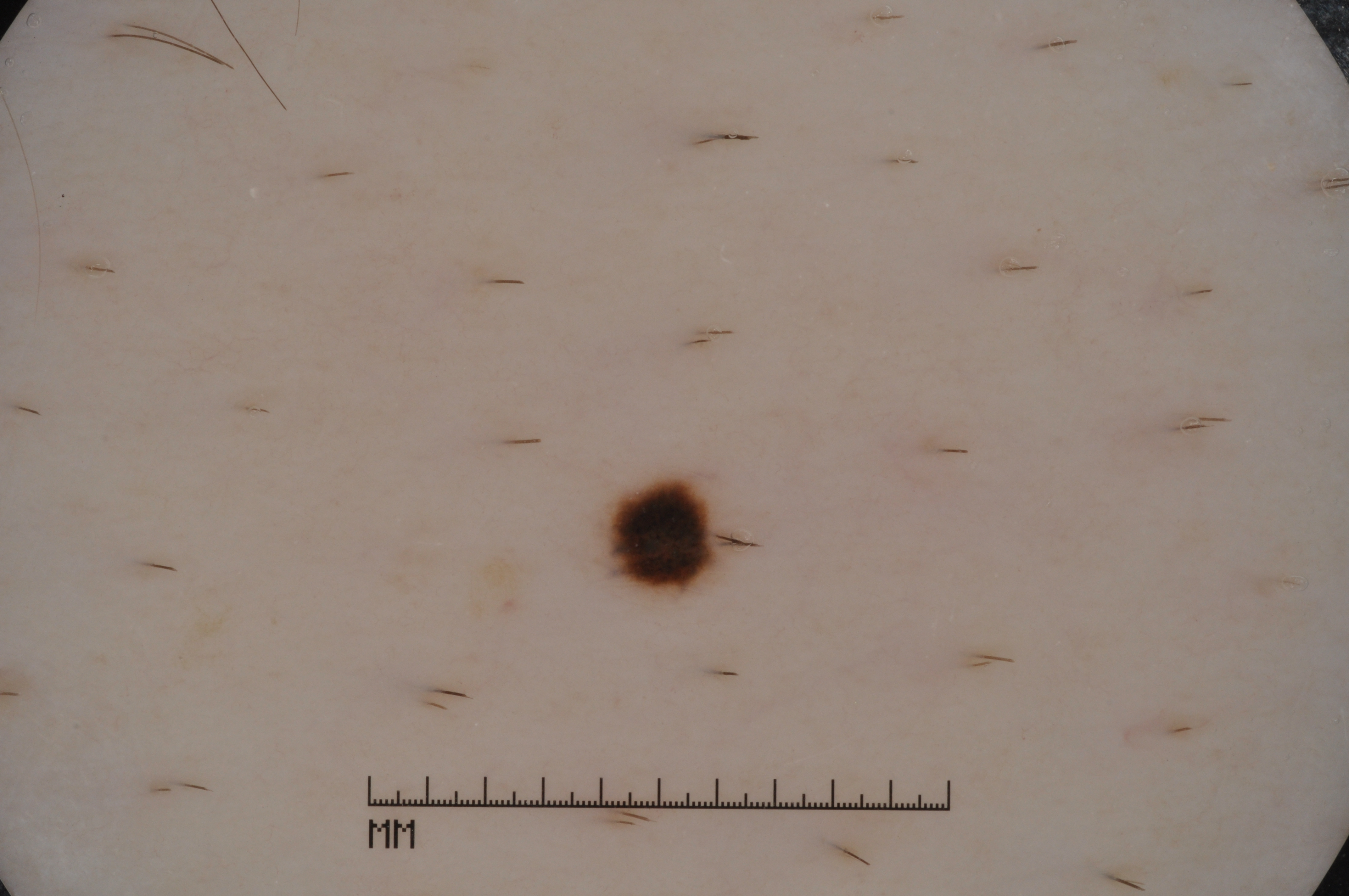Q: How was this image acquired?
A: dermoscopy of a skin lesion
Q: Where is the lesion in the image?
A: x1=595 y1=467 x2=734 y2=605
Q: What did the assessment conclude?
A: a melanocytic nevus, a benign skin lesion